An image taken at an angle.
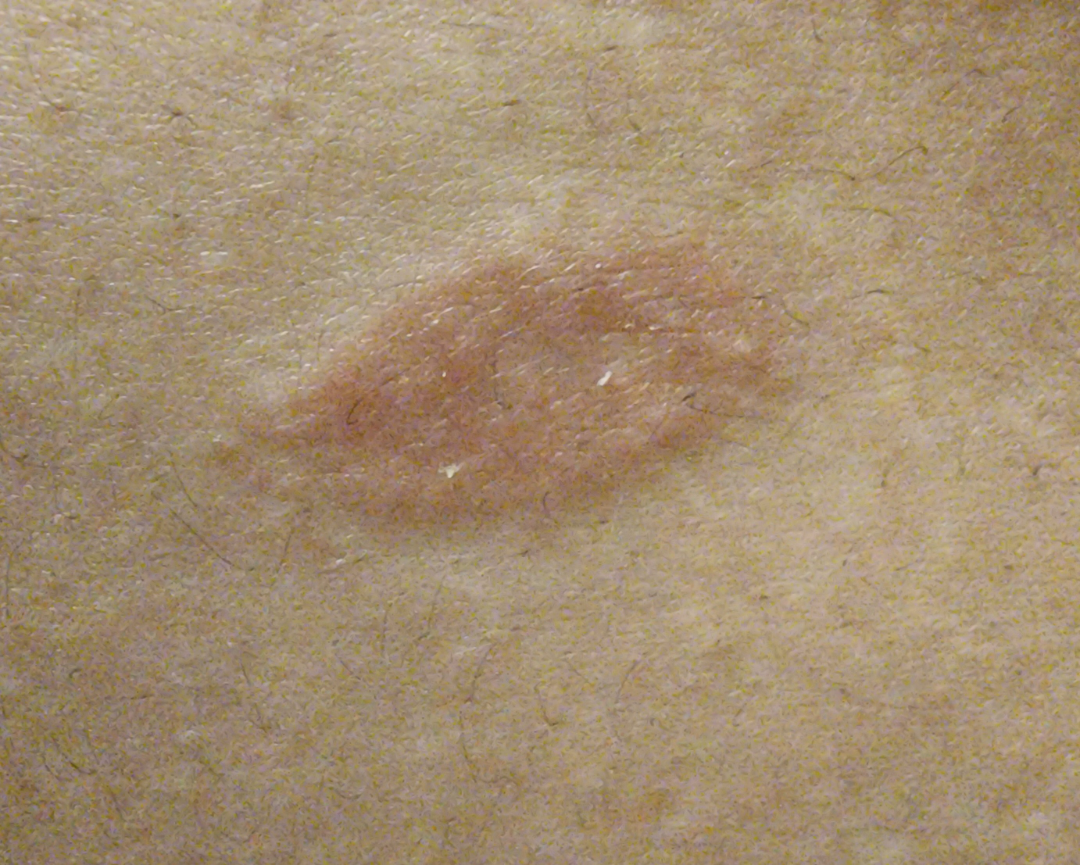Case summary:
• assessment: unable to determine